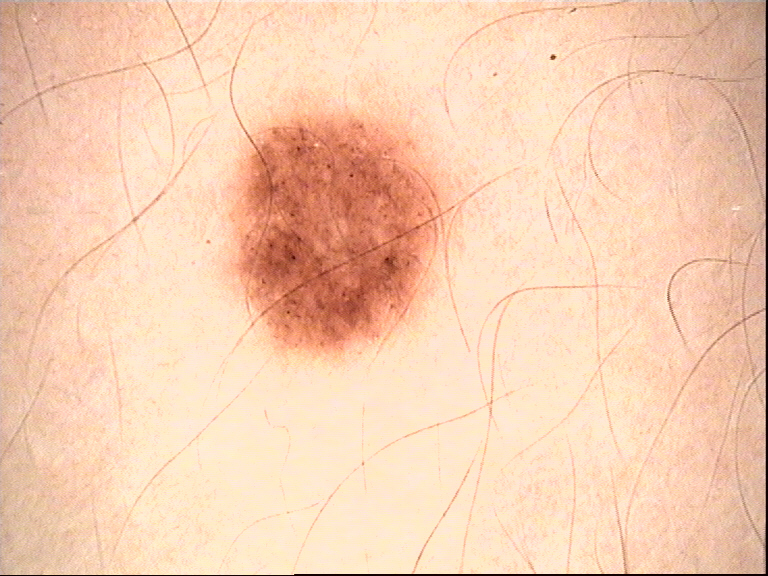label: dysplastic junctional nevus (expert consensus).